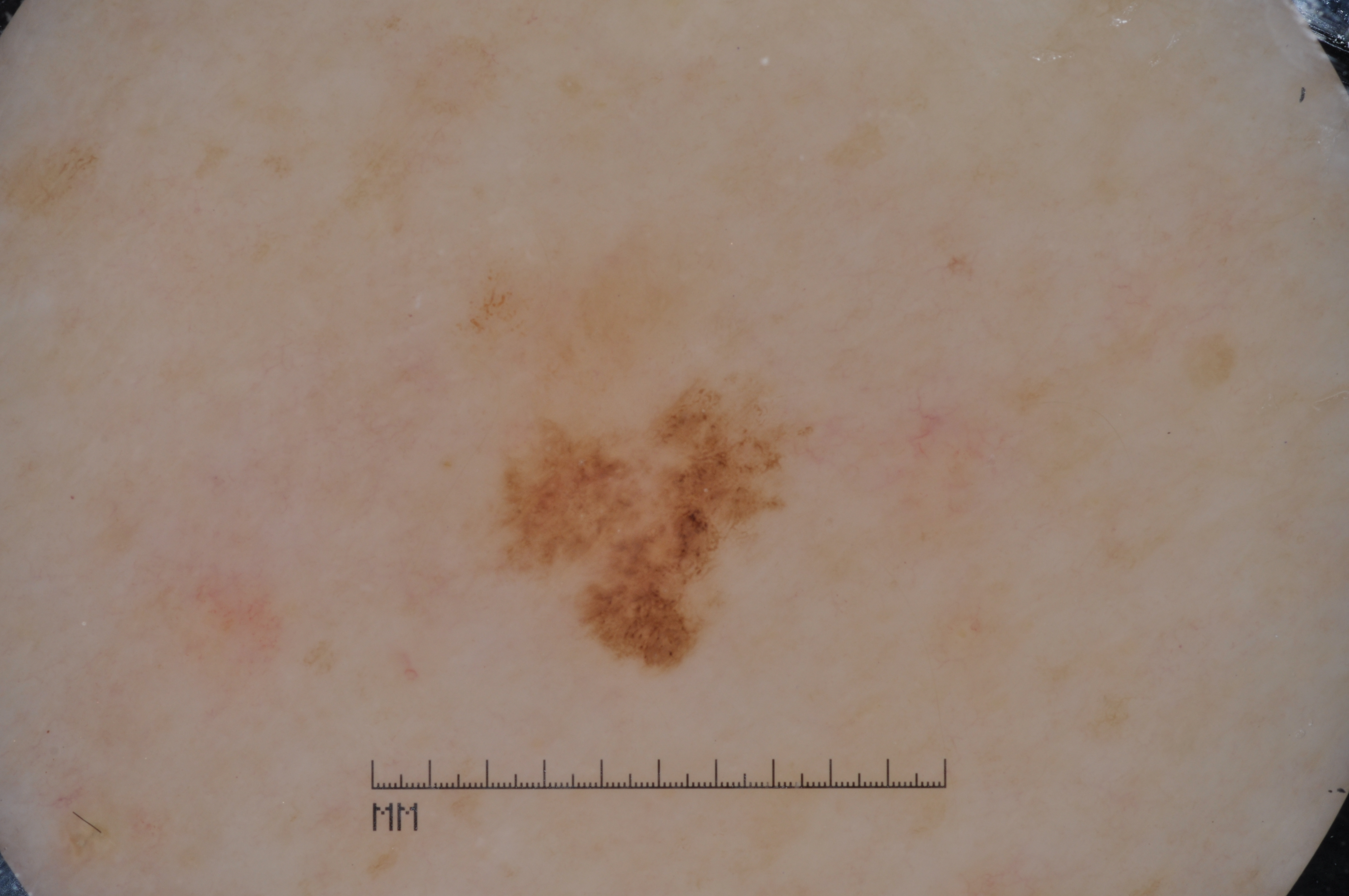A dermoscopic view of a skin lesion.
A female patient approximately 60 years of age.
Dermoscopic examination shows pigment network and milia-like cysts.
In (x1, y1, x2, y2) order, the visible lesion spans <bbox>495, 385, 790, 665</bbox>.
A small lesion occupying a minor part of the field.
Biopsy-confirmed as a melanoma.